A dermoscopic photograph of a skin lesion: 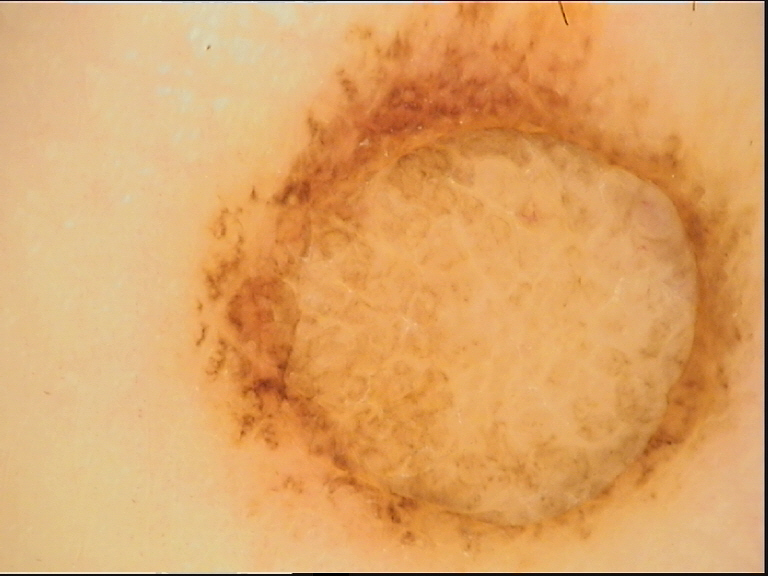The morphology is that of a banal lesion.
Consistent with a dermal nevus.